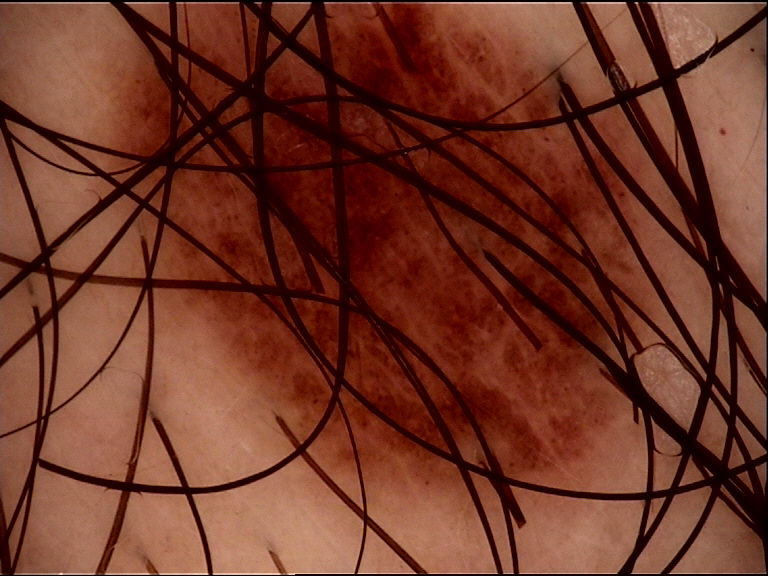modality: dermoscopy; class: dysplastic compound nevus (expert consensus).